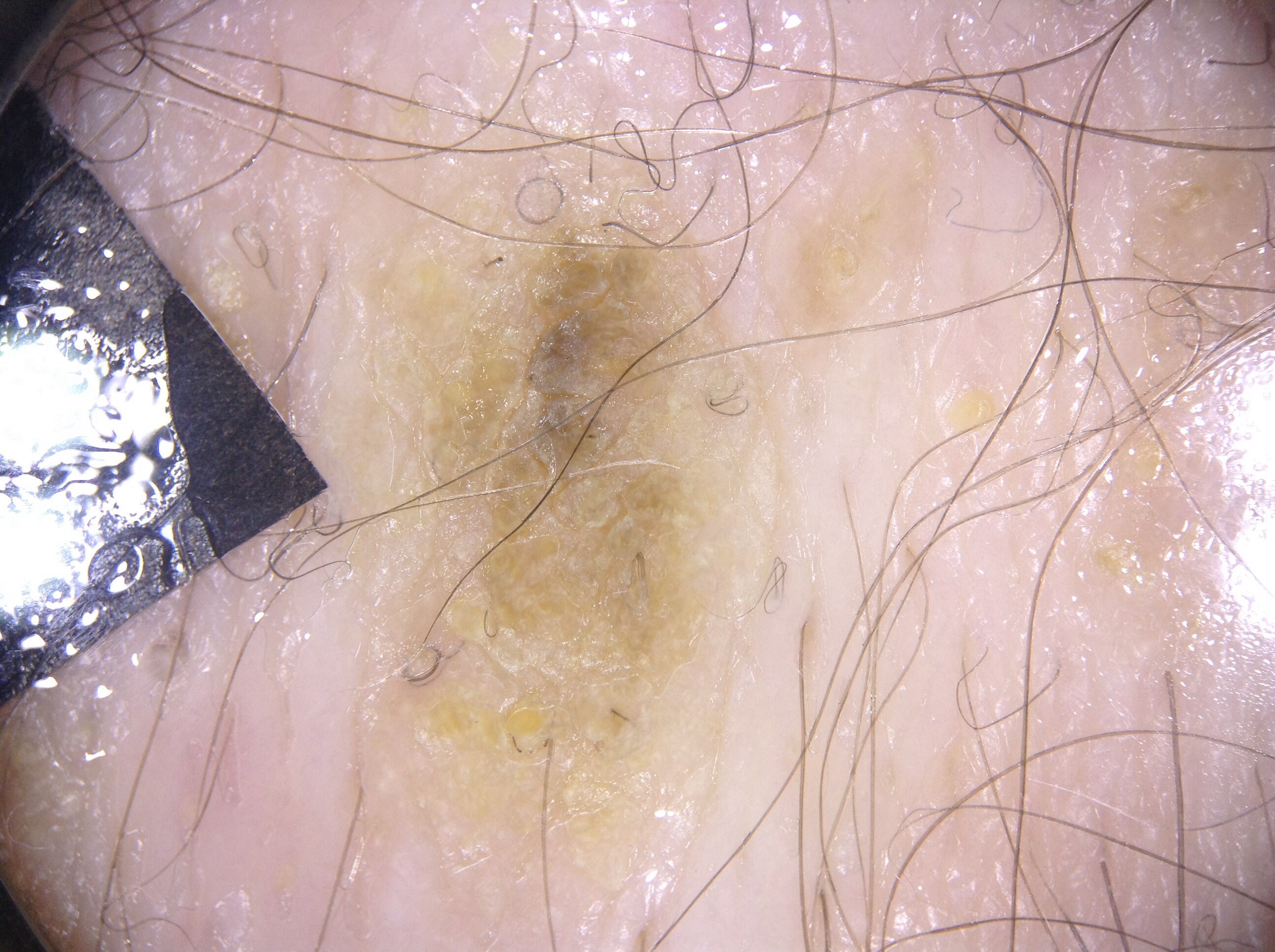subject: male, aged 58-62 | imaging: dermoscopy | lesion bbox: x1=345 y1=146 x2=794 y2=947 | dermoscopic features assessed but absent: negative network, milia-like cysts, streaks, and pigment network | lesion extent: ~24% of the field | diagnosis: a seborrheic keratosis, a benign skin lesion.